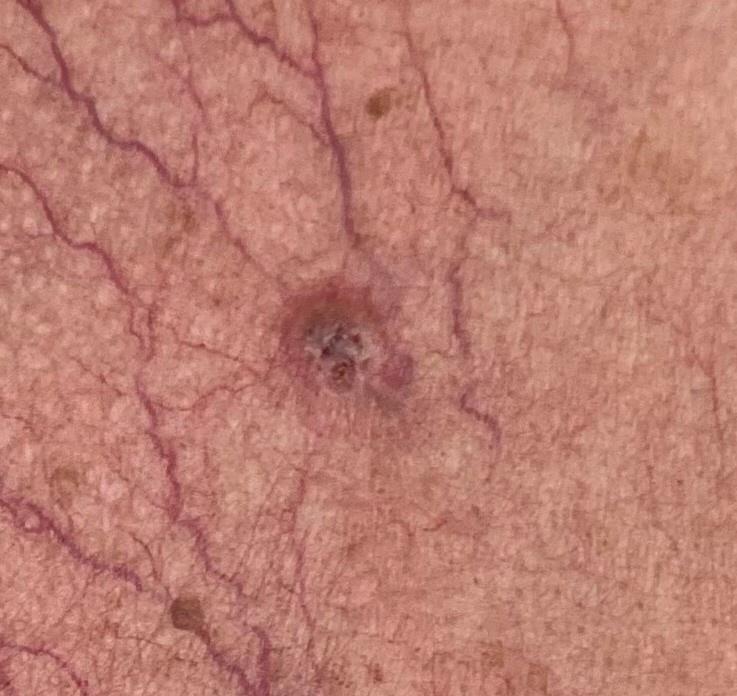image: clinical overview photograph; patient: male, approximately 75 years of age; diagnostic label: Basal cell carcinoma (biopsy-proven).